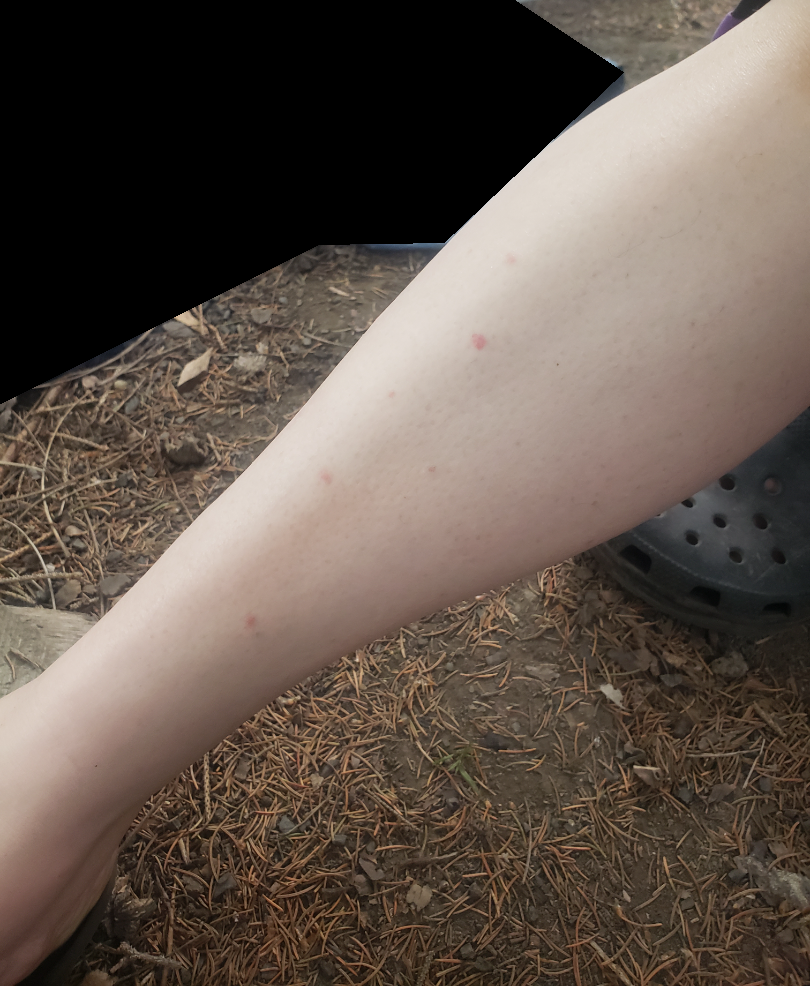The contributor is 40–49, female. The leg is involved. This image was taken at an angle. On remote review of the image: Eczema (52%); Psoriasis (38%); Insect Bite (10%).